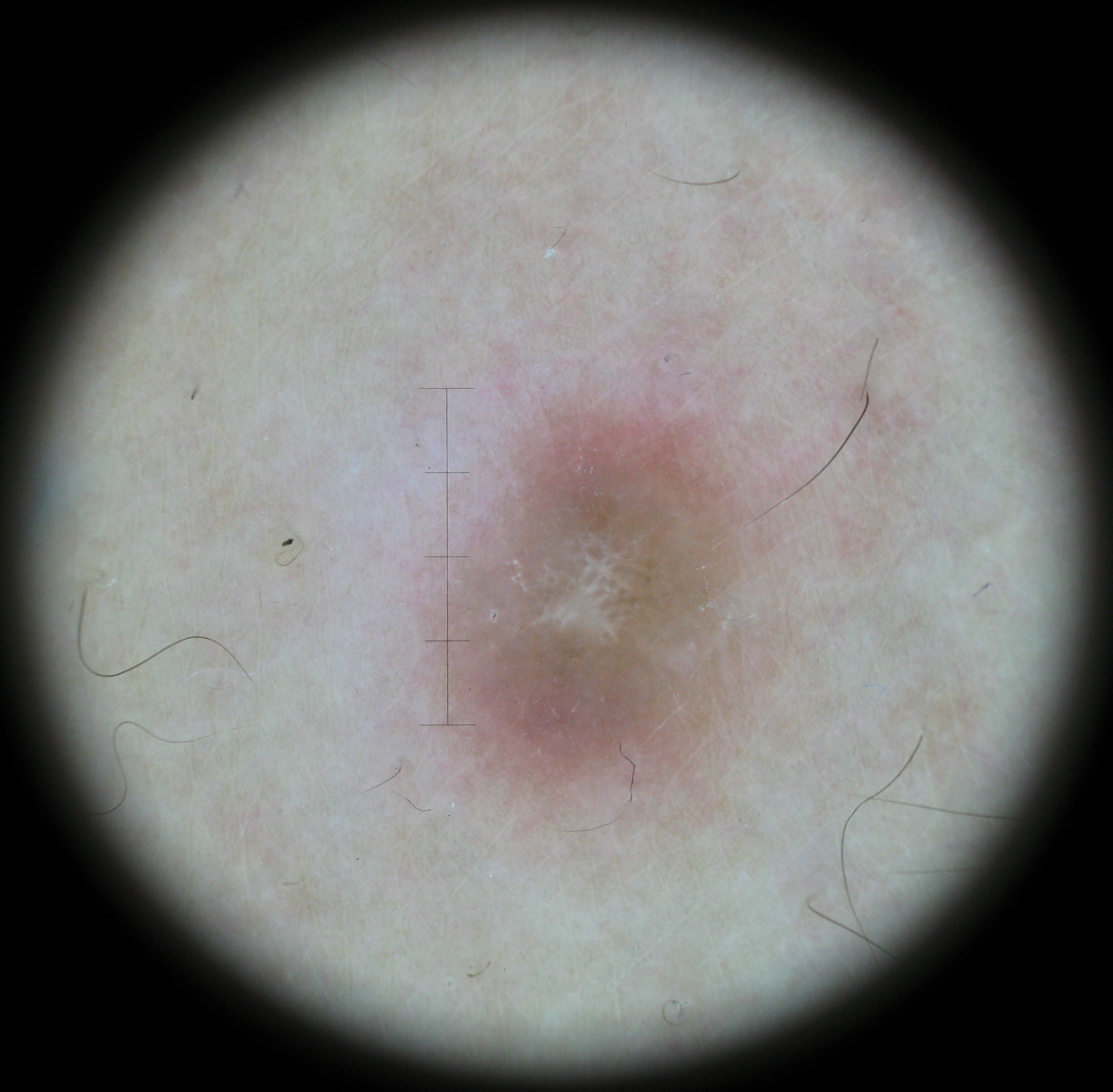{
  "lesion_type": {
    "main_class": "fibro-histiocytic"
  },
  "diagnosis": {
    "name": "dermatofibroma",
    "code": "df",
    "malignancy": "benign",
    "super_class": "non-melanocytic",
    "confirmation": "expert consensus"
  }
}